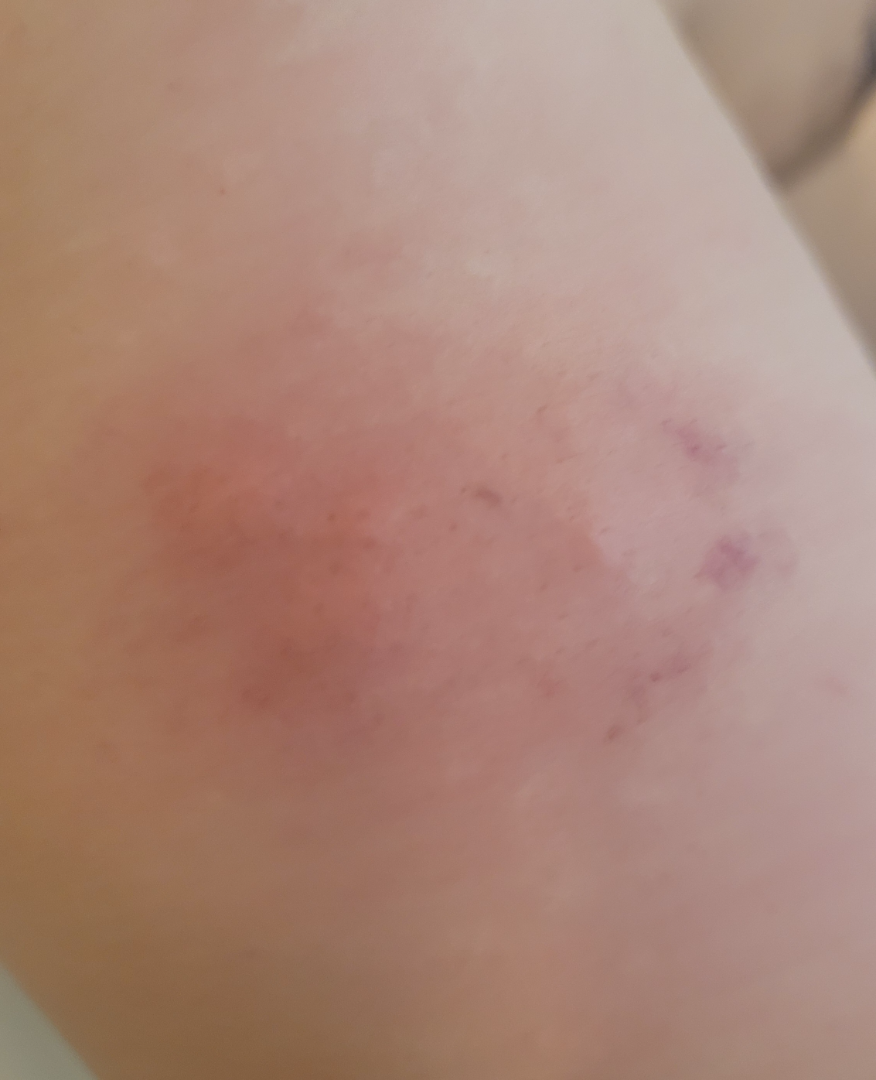The patient considered this a rash.
Male patient, age 40–49.
Located on the back of the hand, arm, head or neck and leg.
The photograph was taken at an angle.
The patient indicates the condition has been present for three to twelve months.
Symptoms reported: itching, bothersome appearance and enlargement.
No constitutional symptoms were reported.
Three dermatologists each reviewed the case: Abscess, Cellulitis and Cyst were each considered, in no particular order.